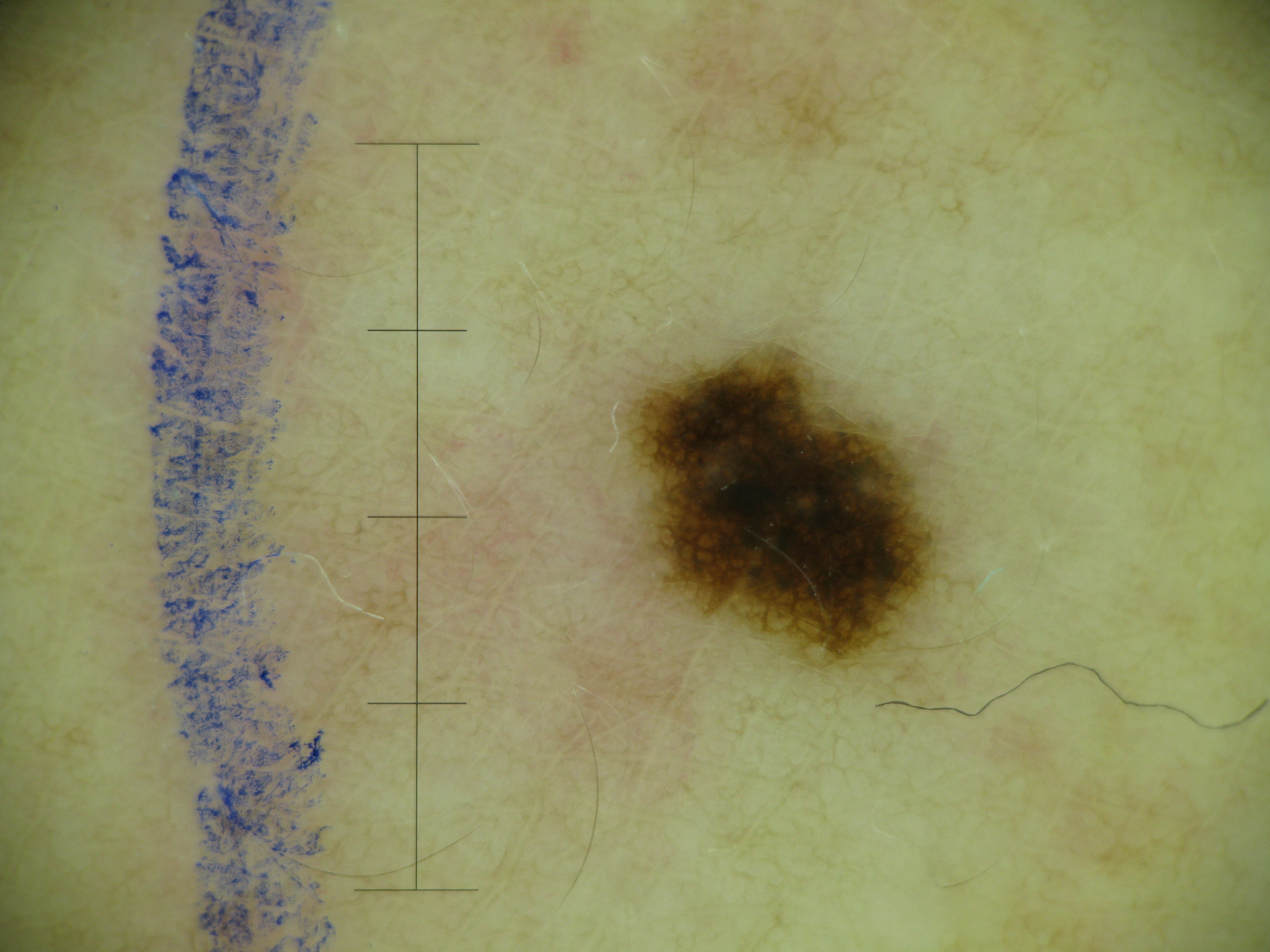Q: What was the diagnostic impression?
A: dysplastic junctional nevus (expert consensus)